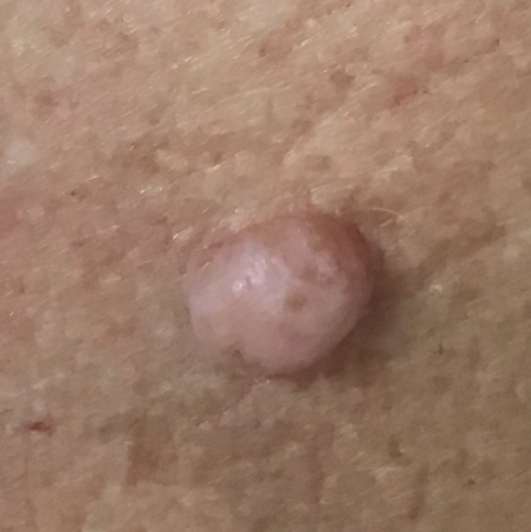image type = smartphone clinical photo; subject = 60 years old; region = the chest; reported symptoms = elevation, growth / no bleeding; diagnostic label = nevus (clinical consensus).